A dermoscopic photograph of a skin lesion.
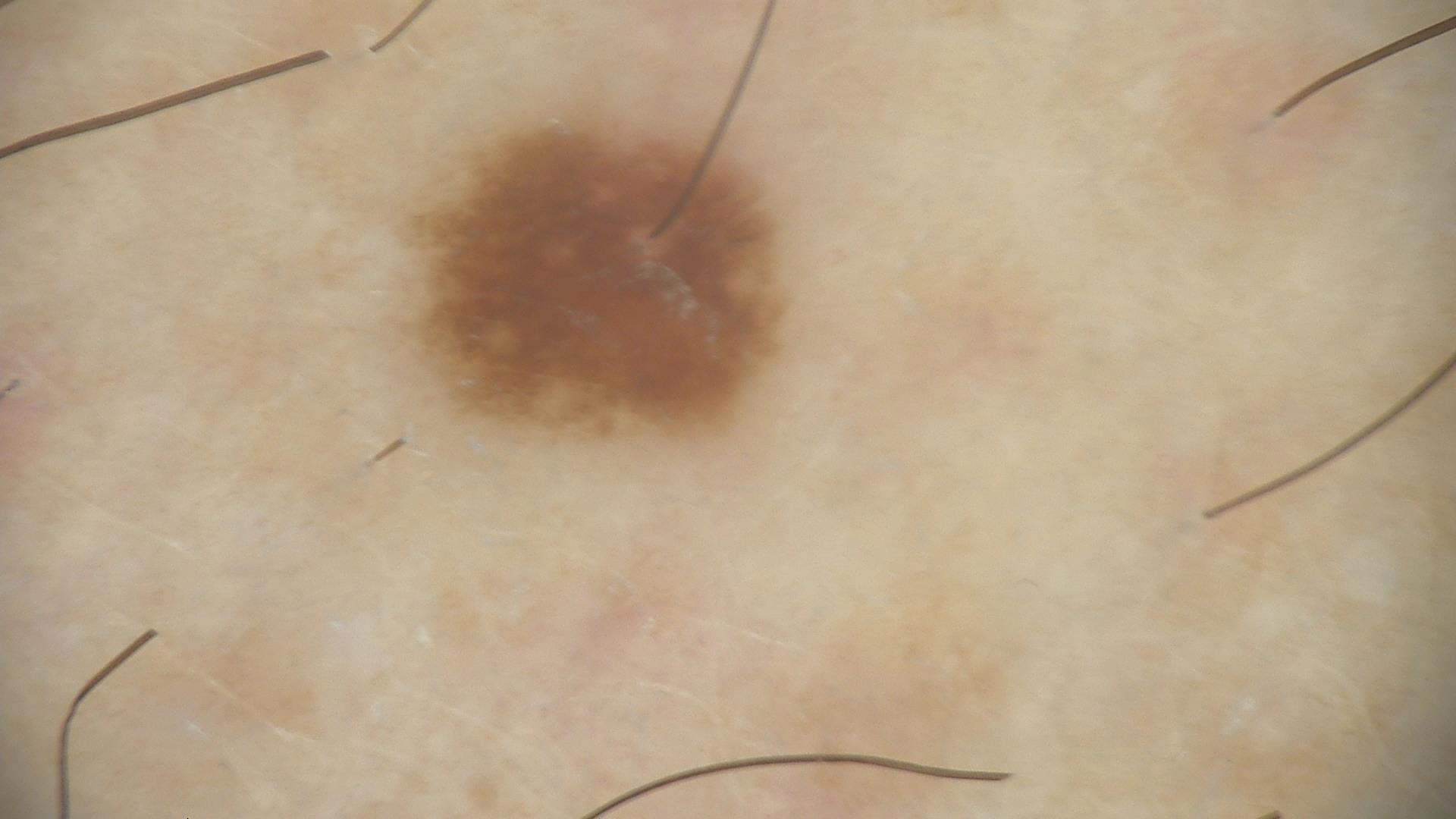{"diagnosis": {"name": "dysplastic junctional nevus", "code": "jd", "malignancy": "benign", "super_class": "melanocytic", "confirmation": "expert consensus"}}